This image was taken at an angle · Fitzpatrick skin type II; human graders estimated MST 1 or 2 (two reviewer pools) · the condition has been present for less than one week · the patient described the issue as acne · the subject is 50–59, female · the affected area is the head or neck · texture is reported as raised or bumpy and fluid-filled · no constitutional symptoms were reported:
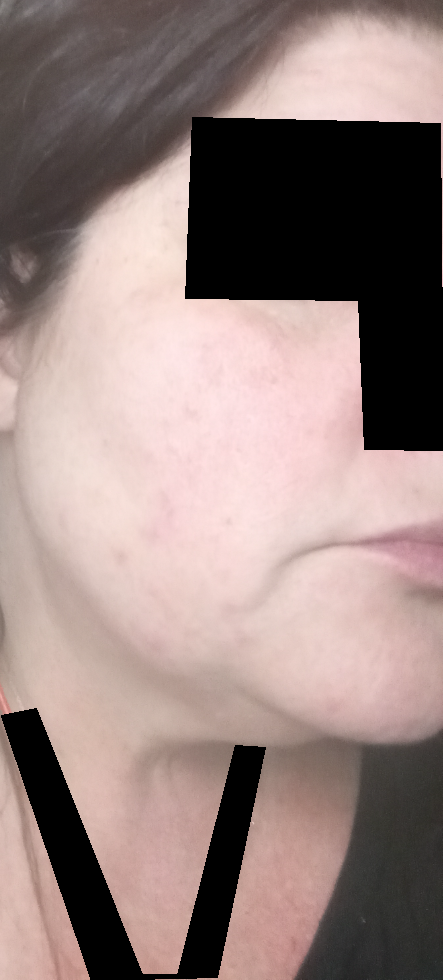assessment: most consistent with Rosacea; an alternative is Acne.